The lesion involves the front of the torso · close-up view.
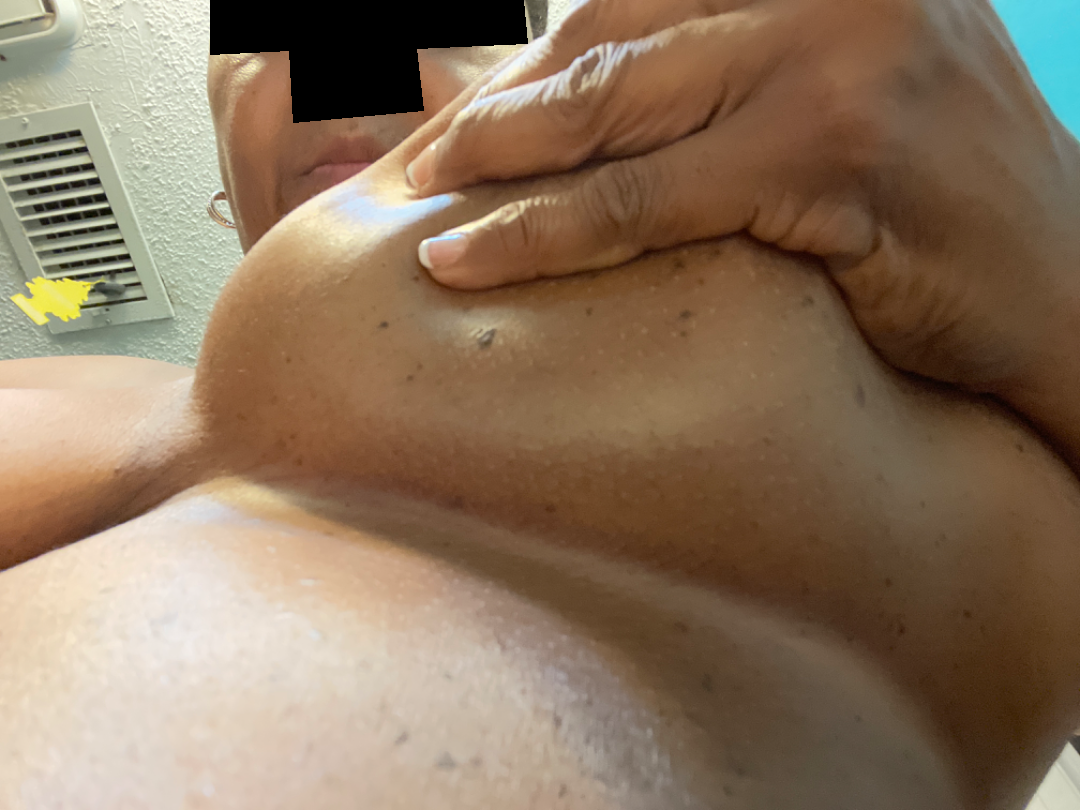| feature | finding |
|---|---|
| assessment | indeterminate |